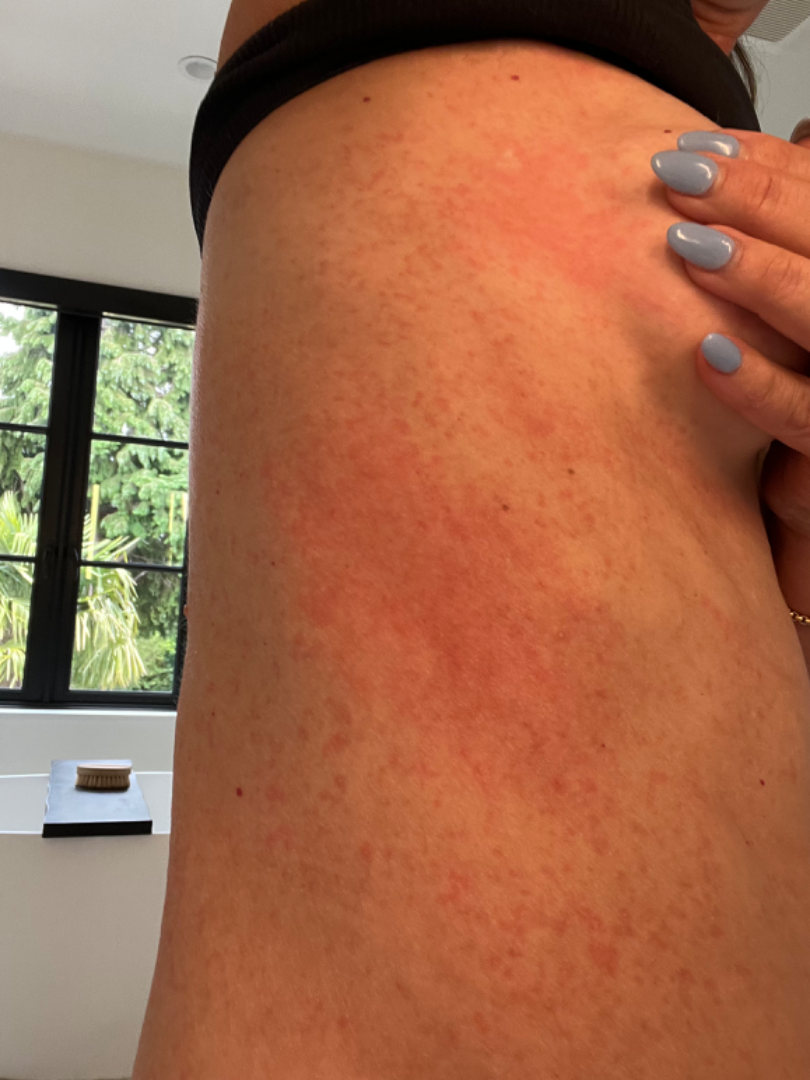Q: What was the assessment?
A: unable to determine
Q: What is the affected area?
A: head or neck, front of the torso, back of the torso and arm
Q: Fitzpatrick or Monk tone?
A: Fitzpatrick phototype III; lay reviewers estimated Monk skin tone scale 4 (US pool) or 2 (India pool)
Q: Patient's own categorization?
A: a rash
Q: How does the lesion feel?
A: flat
Q: Reported symptoms?
A: itching
Q: How was the photo taken?
A: close-up
Q: When did this start?
A: about one day